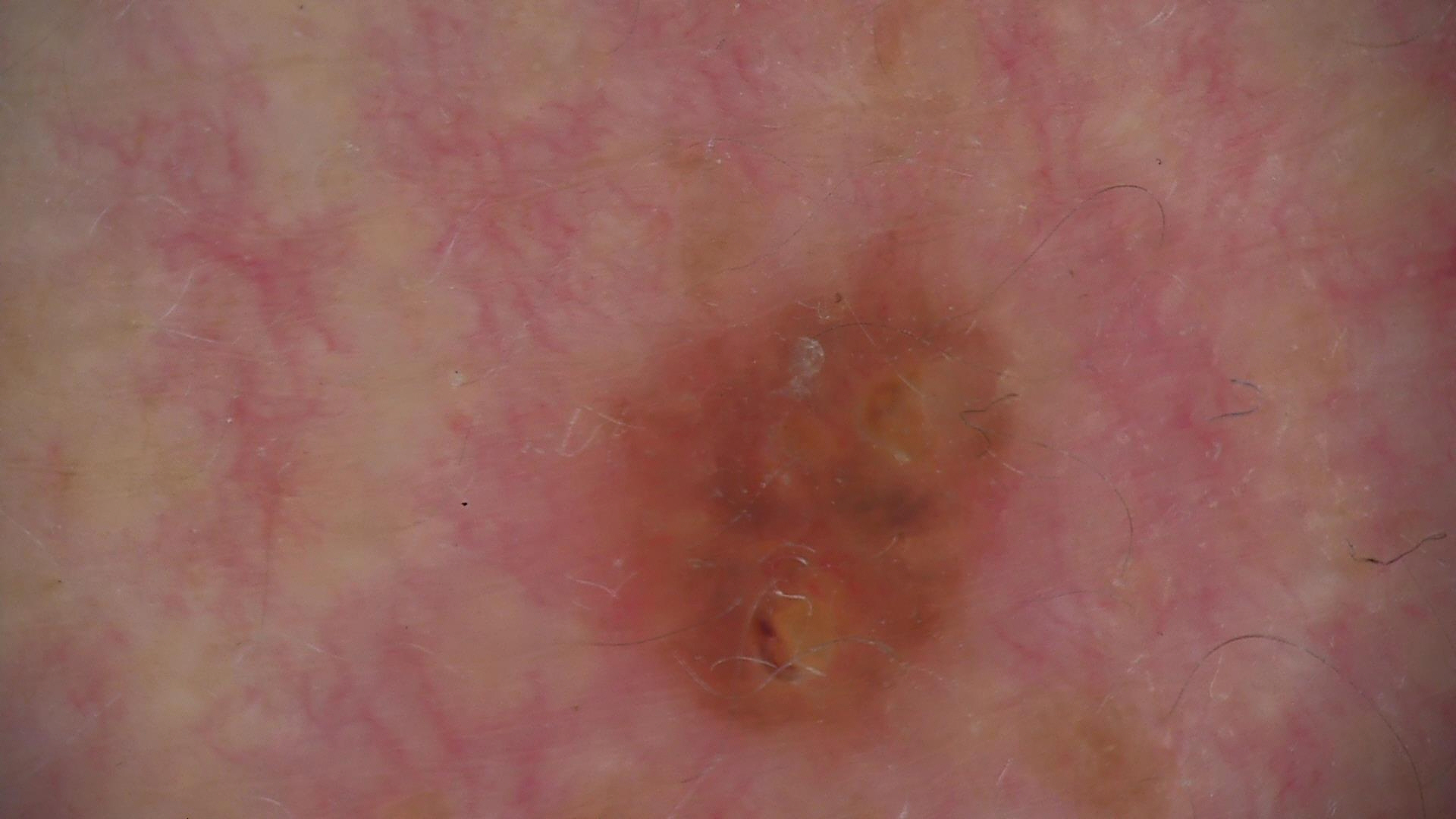Dermoscopy of a skin lesion. The diagnostic label was a keratinocytic, benign lesion — a seborrheic keratosis.